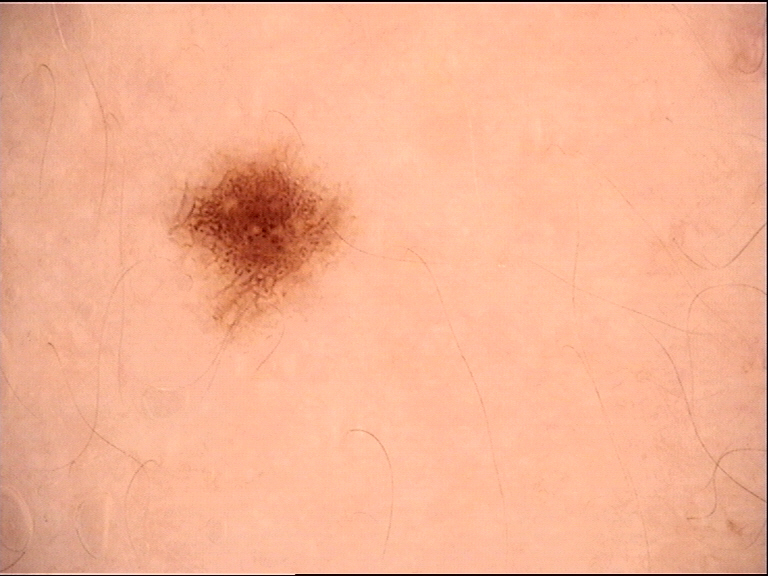A dermoscopic close-up of a skin lesion. Consistent with a banal lesion — a junctional nevus.